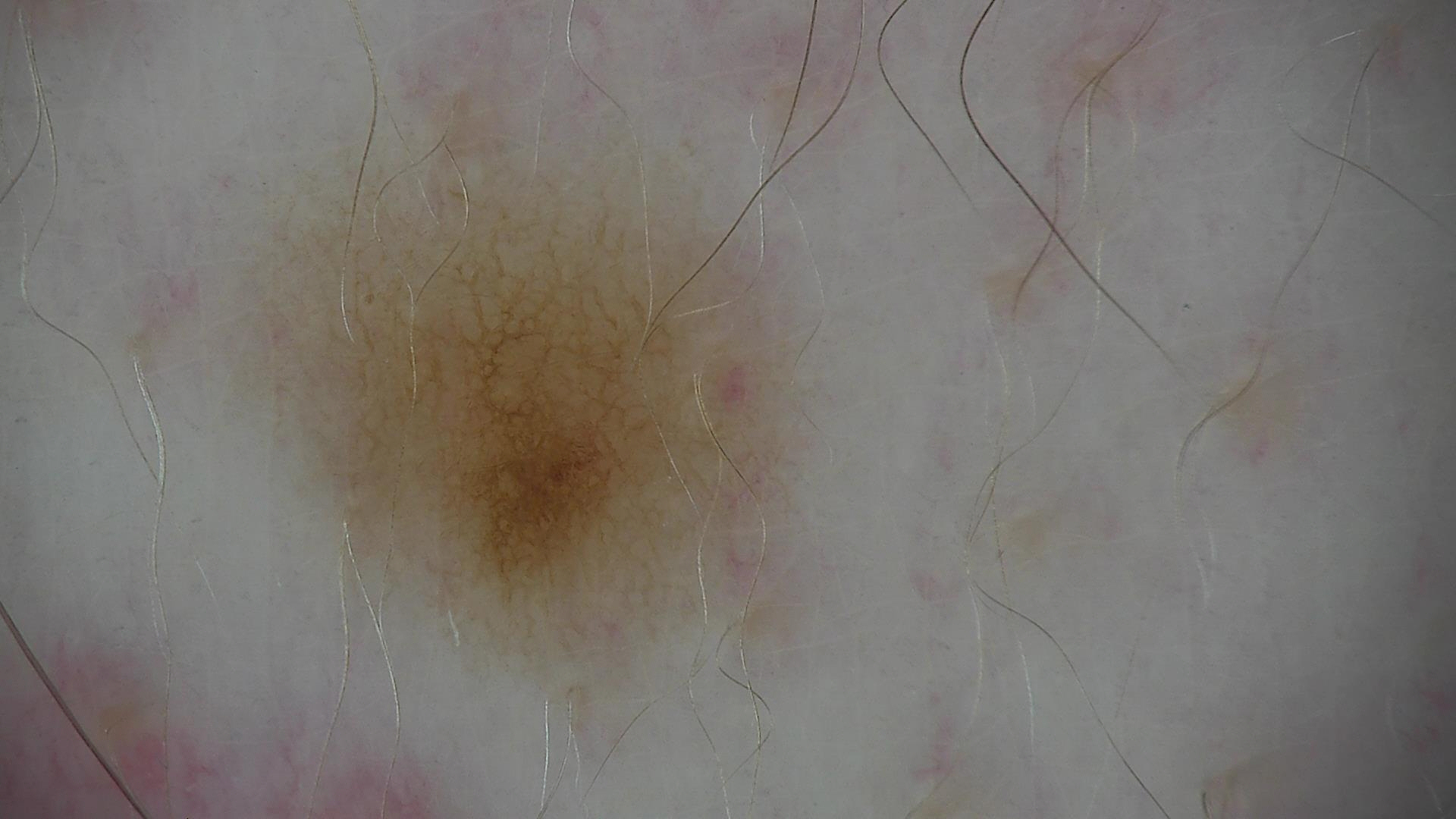  image: dermoscopy
  diagnosis:
    name: dysplastic junctional nevus
    code: jd
    malignancy: benign
    super_class: melanocytic
    confirmation: expert consensus